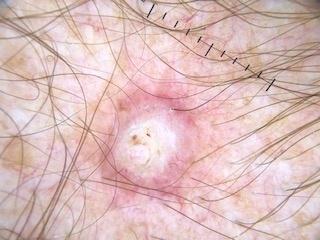{
  "image": "contact-polarized dermoscopy",
  "patient": {
    "age_approx": 75,
    "sex": "male"
  },
  "lesion_location": {
    "region": "the trunk"
  },
  "diagnosis": {
    "name": "Basal cell carcinoma",
    "malignancy": "malignant",
    "confirmation": "histopathology",
    "lineage": "adnexal"
  }
}